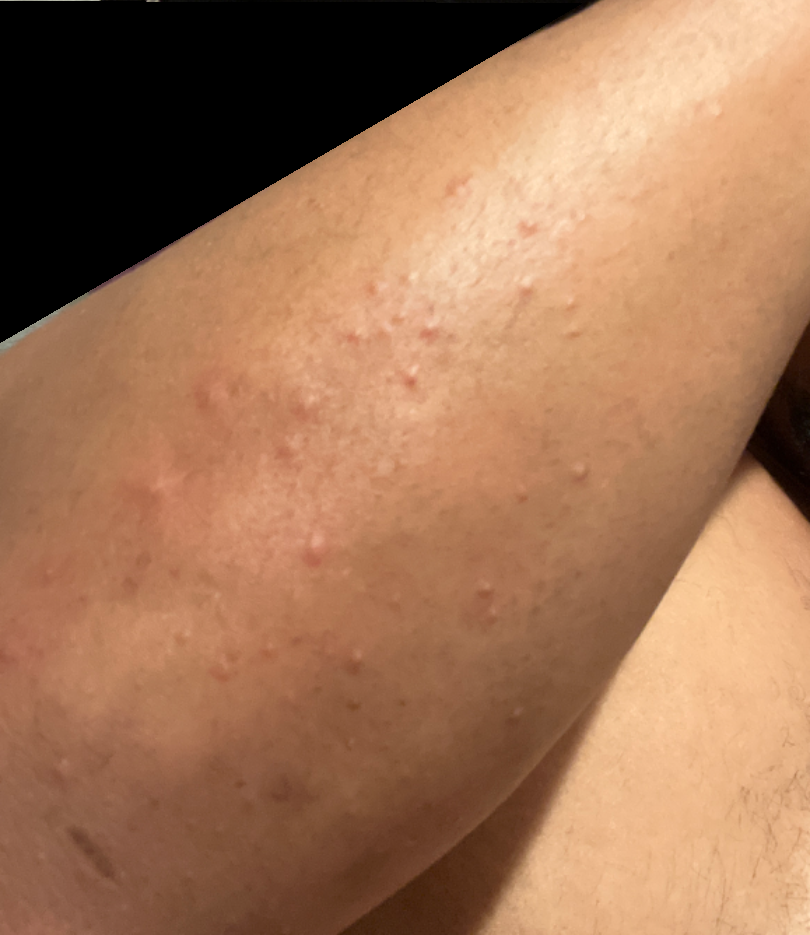The image was not sufficient for the reviewer to characterize the skin condition. Close-up view.